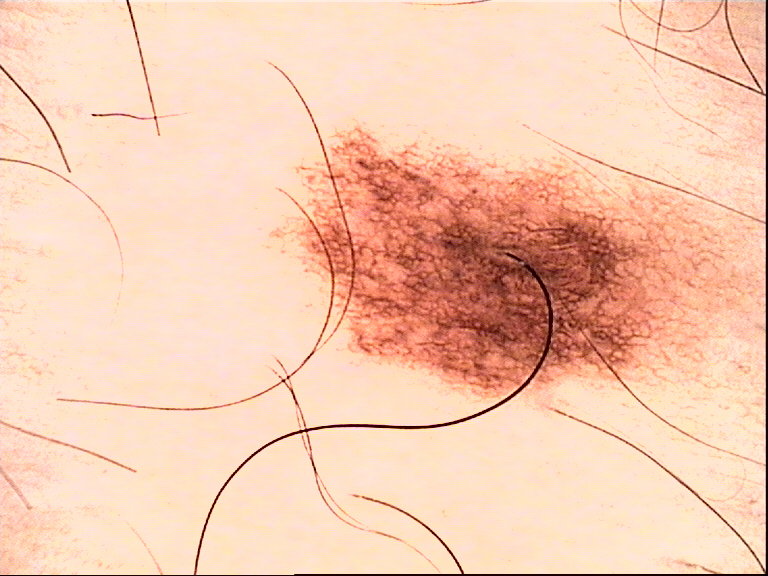A dermoscopic image of a skin lesion. Diagnosed as a dysplastic junctional nevus.